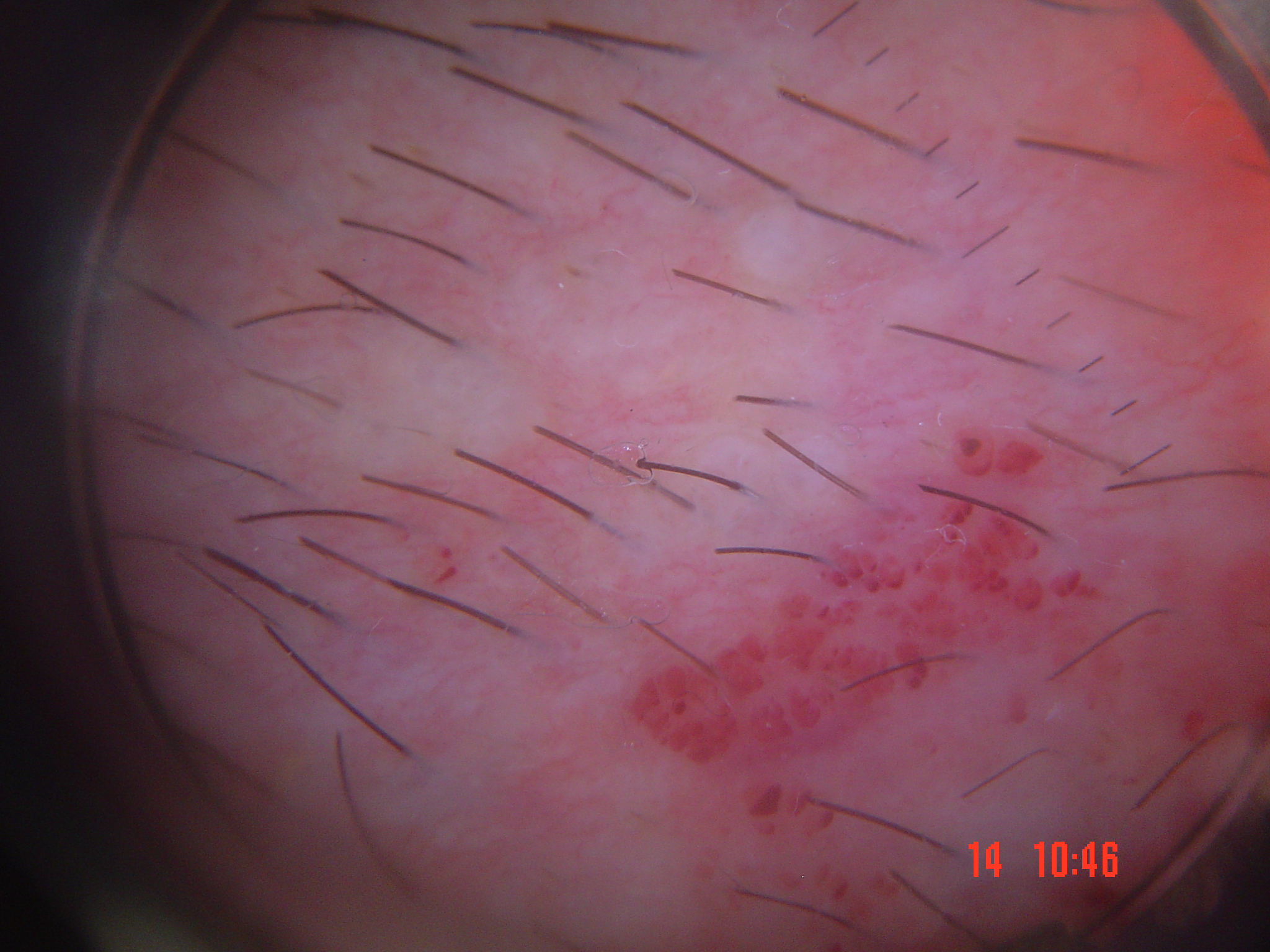A skin lesion imaged with a dermatoscope. Diagnosed as a vascular lesion — a lymphangioma.